A skin lesion imaged with a dermatoscope.
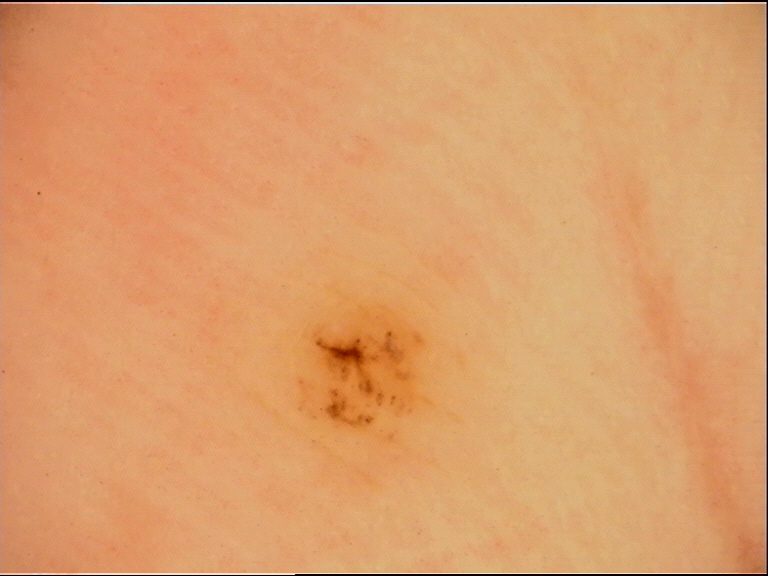{
  "lesion_type": {
    "main_class": "banal",
    "pattern": "junctional"
  },
  "diagnosis": {
    "name": "acral junctional nevus",
    "code": "ajb",
    "malignancy": "benign",
    "super_class": "melanocytic",
    "confirmation": "expert consensus"
  }
}